A dermoscopic image of a skin lesion: 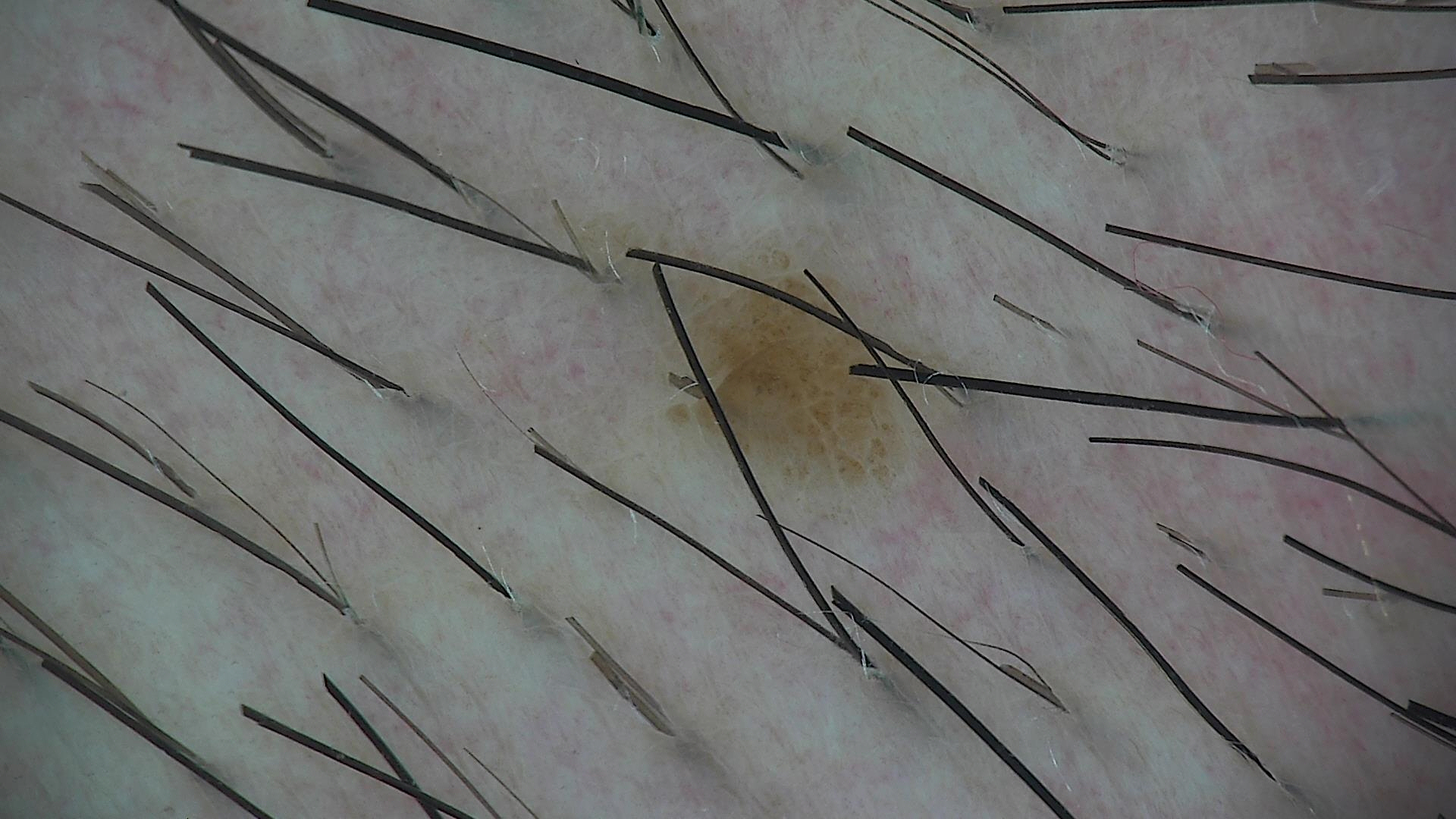Diagnosed as a dysplastic junctional nevus.